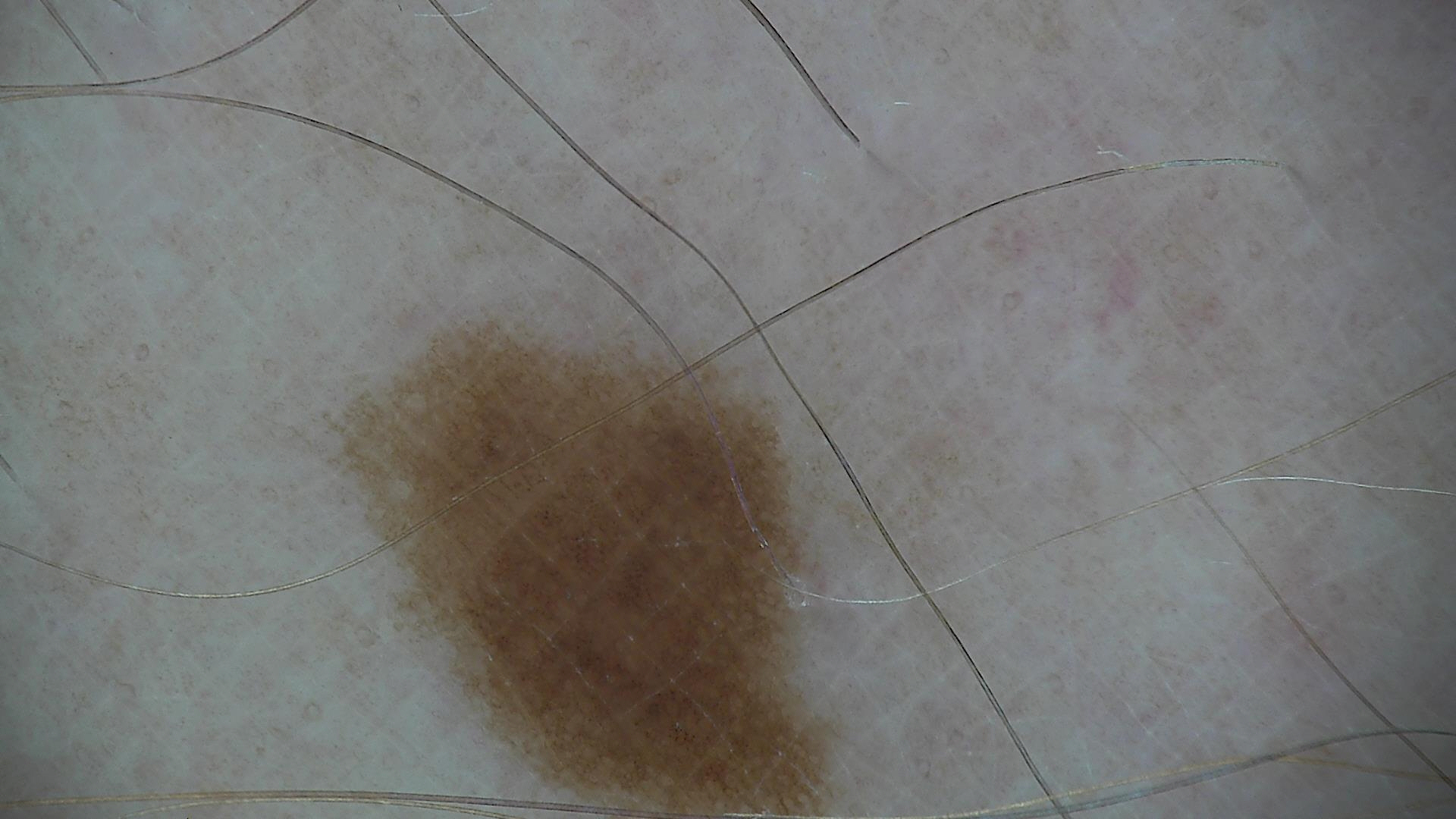modality = dermatoscopy | assessment = dysplastic junctional nevus (expert consensus).